The lesion is described as fluid-filled, raised or bumpy and rough or flaky · self-categorized by the patient as a rash · female patient, age 40–49 · the photo was captured at an angle · located on the leg · skin tone: Fitzpatrick phototype III; human graders estimated MST 2 or 6 (two reviewer pools disagreed) · no constitutional symptoms were reported.
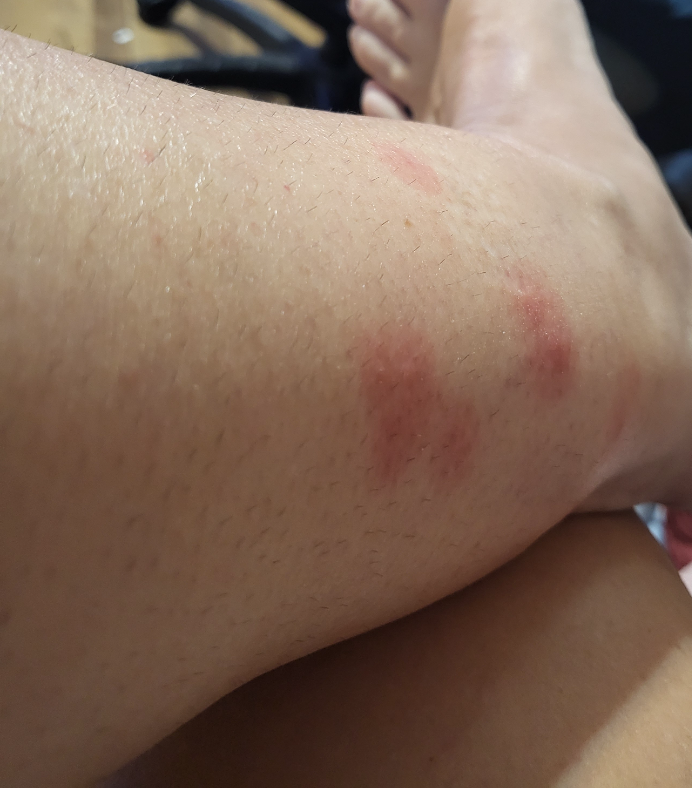impression: Insect Bite (most likely); Localized skin infection (considered); Allergic Contact Dermatitis (considered)